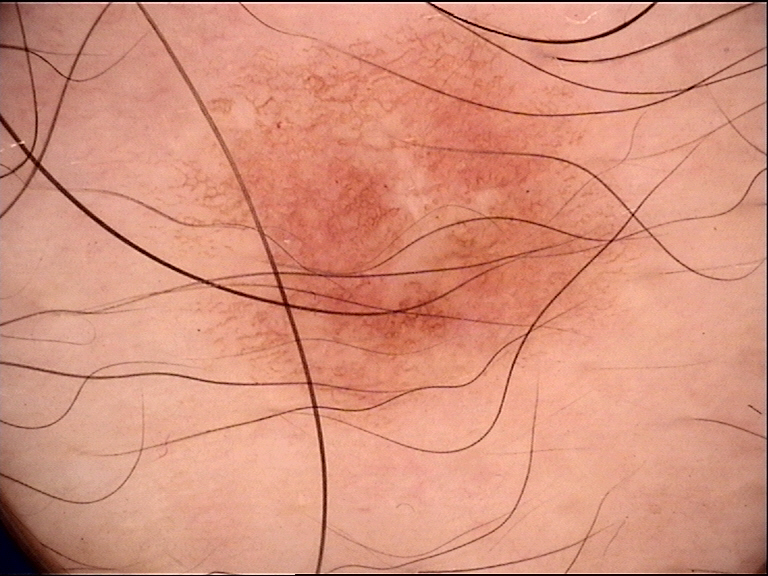diagnostic label = dysplastic junctional nevus (expert consensus).